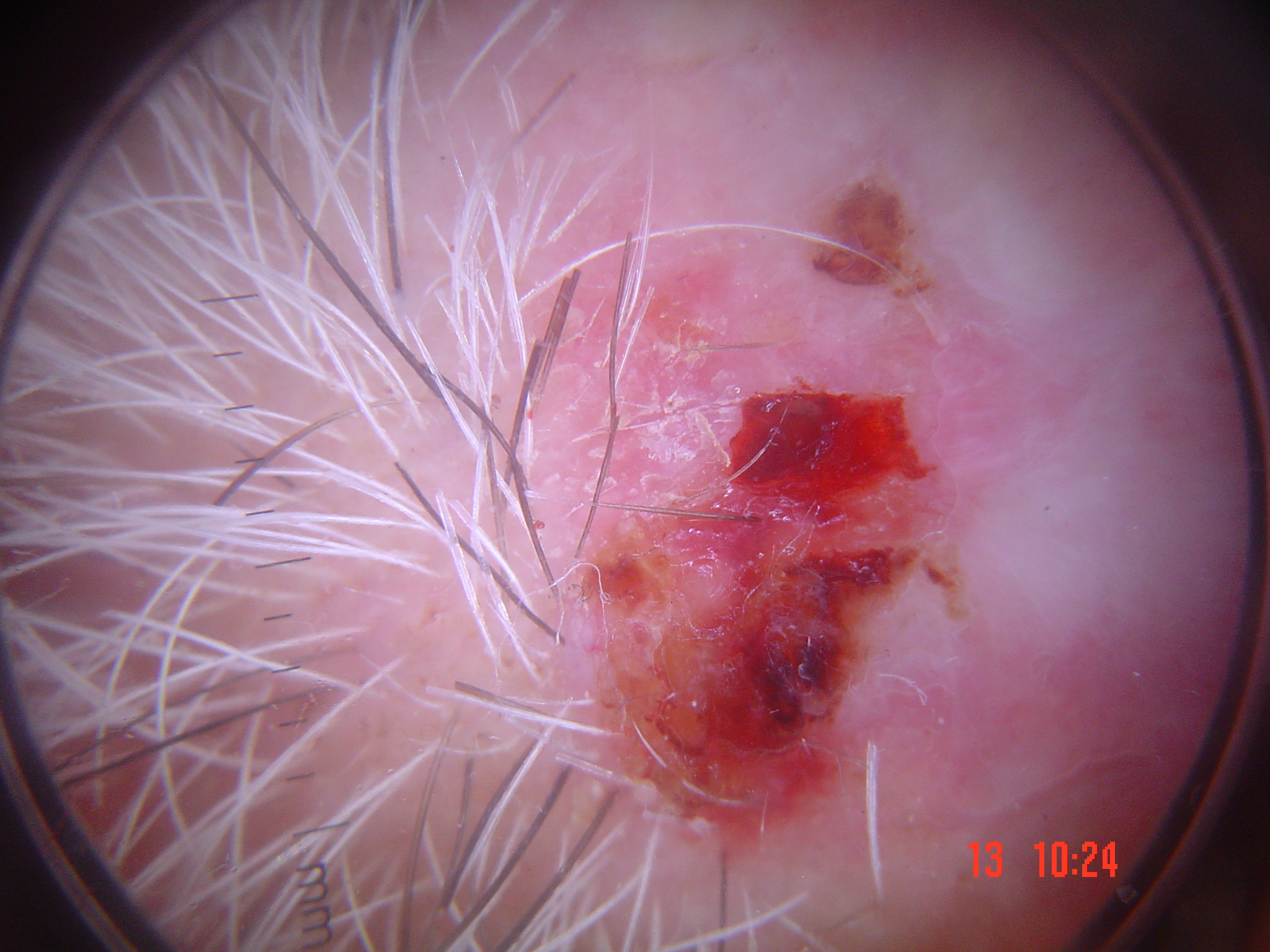Case:
A dermatoscopic image of a skin lesion. The morphology is that of a keratinocytic lesion.
Conclusion:
The biopsy diagnosis was a malignancy — a squamous cell carcinoma.